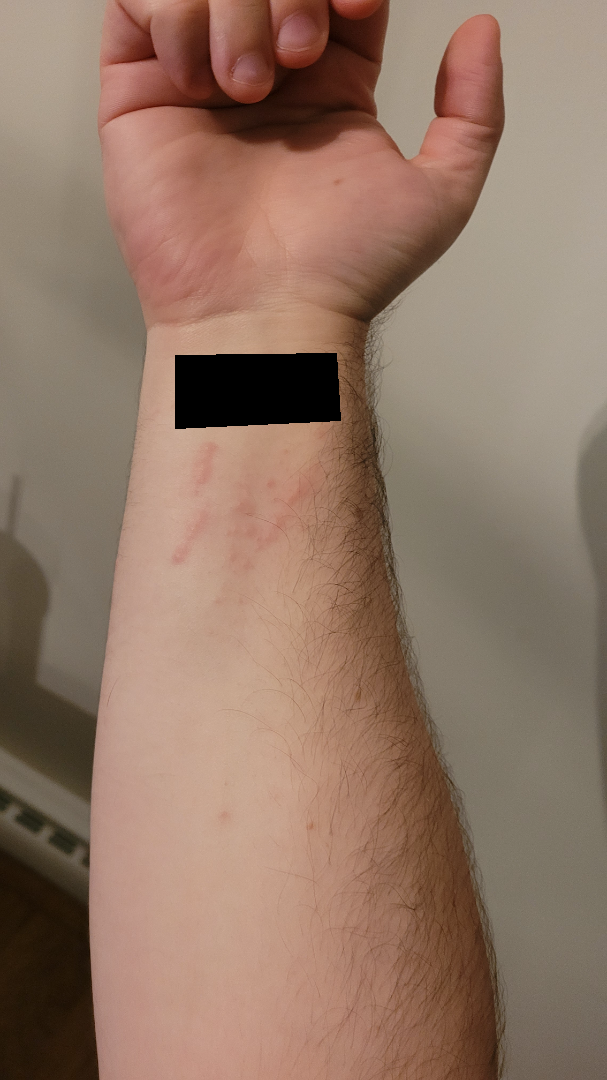| key | value |
|---|---|
| assessment | could not be assessed |